The contributor is 30–39, female · reported lesion symptoms include itching · the arm is involved · the patient considered this a rash · the photograph is a close-up of the affected area · present for one to four weeks: 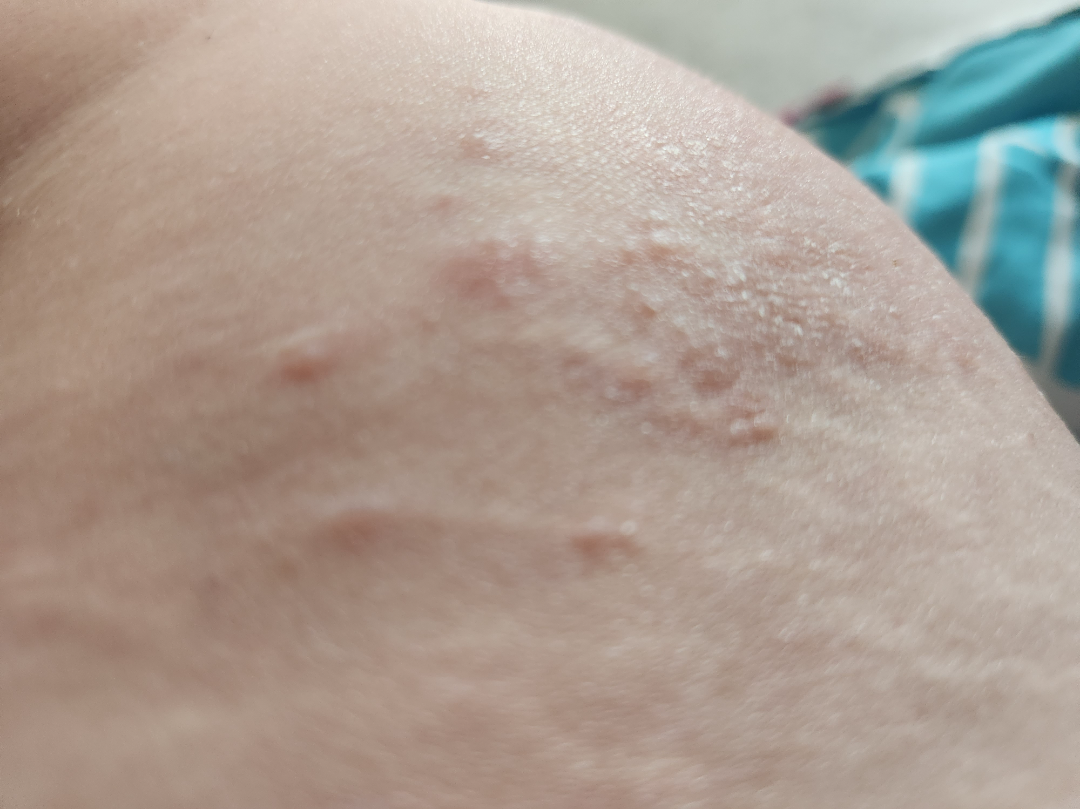On dermatologist assessment of the image, Urticaria (0.30); Eczema (0.22); Allergic Contact Dermatitis (0.22); Pruritic urticarial papules and plaques of pregnancy (0.15); Scabies (0.10).